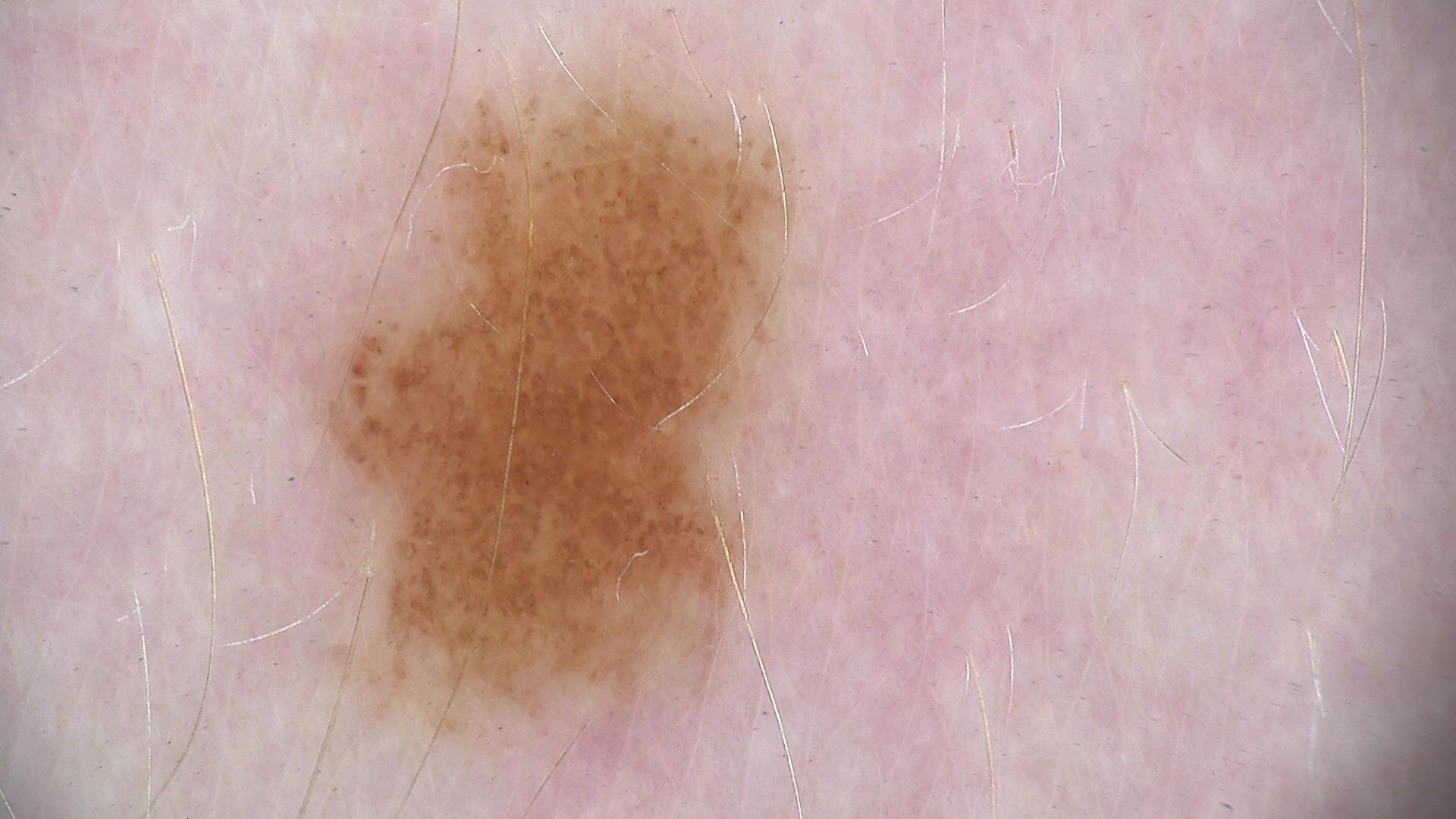modality = dermoscopy, assessment = dysplastic junctional nevus (expert consensus).